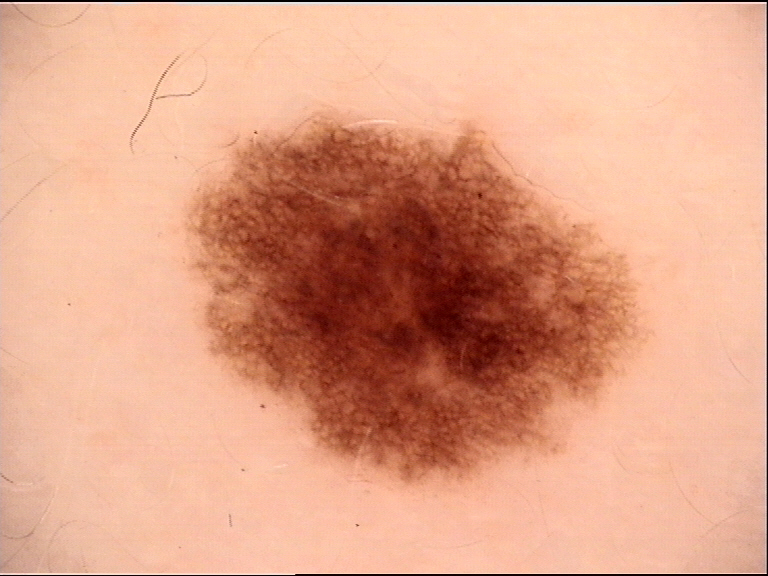modality: dermoscopy | label: dysplastic junctional nevus (expert consensus).